The photograph was taken at a distance, the patient is a female aged 18–29, the arm is involved:
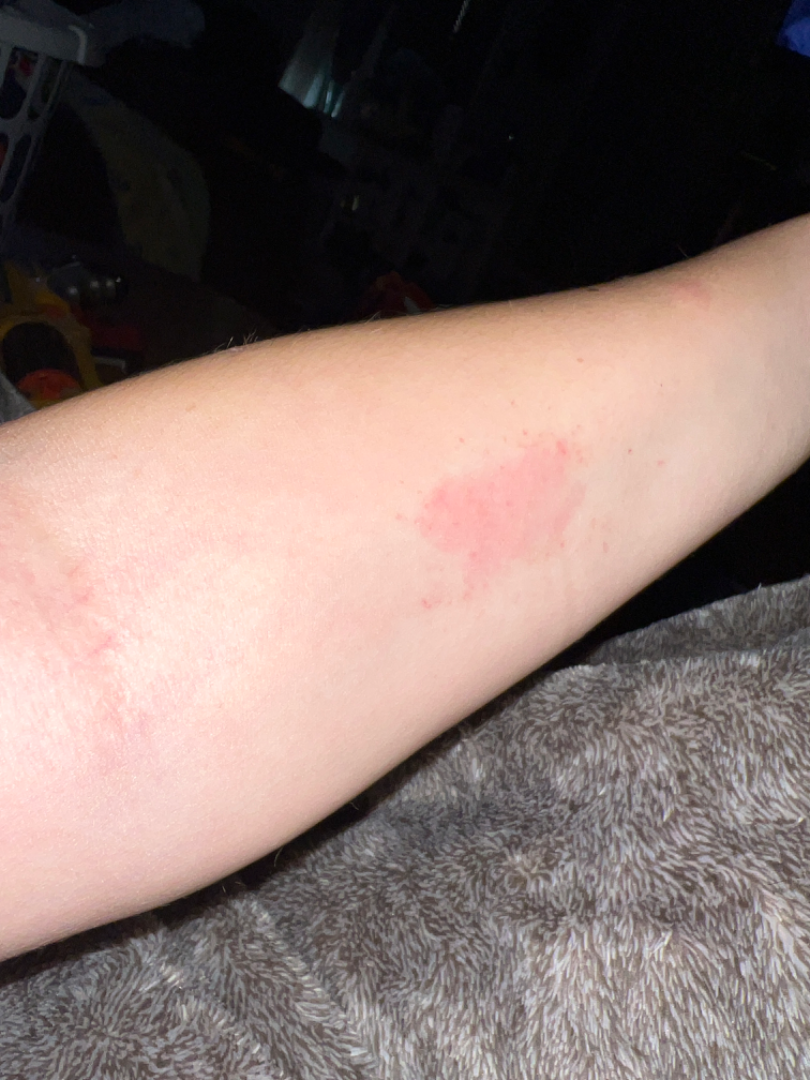Findings:
• skin tone · Fitzpatrick phototype II
• patient describes the issue as · a rash
• history · less than one week
• patient-reported symptoms · itching and enlargement
• lesion texture · raised or bumpy
• systemic symptoms · fatigue
• clinical impression · single-reviewer assessment: Eczema, Hypersensitivity and Allergic Contact Dermatitis were considered with similar weight